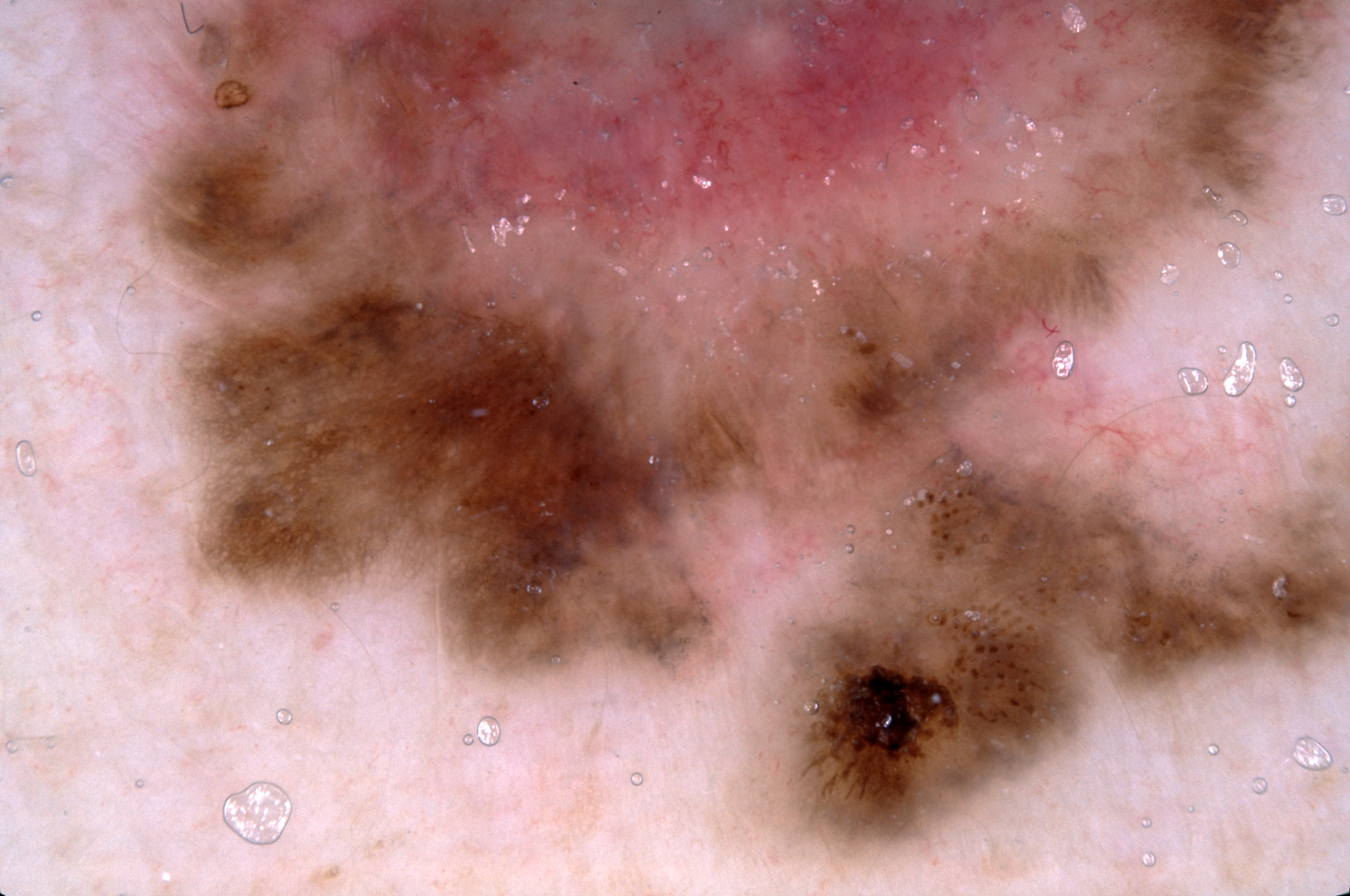Q: What is the imaging modality?
A: dermoscopy of a skin lesion
Q: Who is the patient?
A: male, roughly 55 years of age
Q: Lesion extent?
A: ~73% of the field
Q: What does dermoscopy show?
A: pigment network
Q: Where is the lesion located?
A: bbox(121, 1, 1346, 874)
Q: What is this lesion?
A: a melanoma, a skin cancer